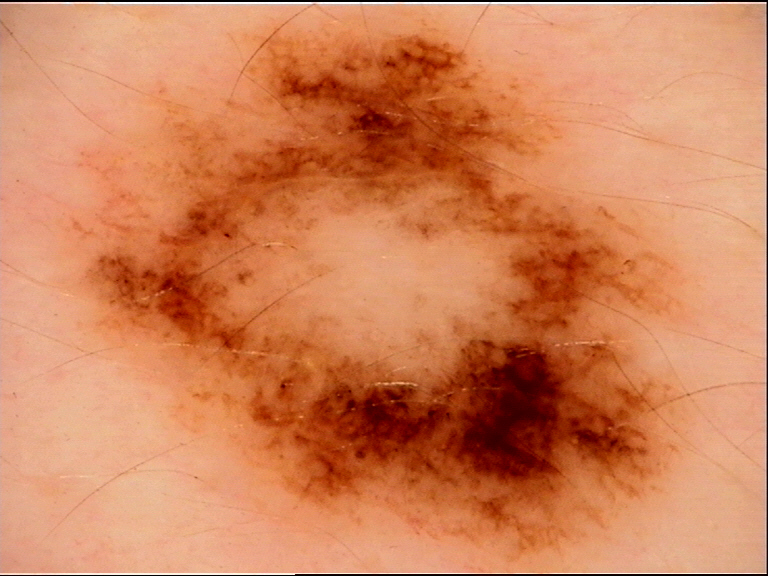* diagnostic label — dysplastic junctional nevus (expert consensus)